A dermatoscopic image of a skin lesion — 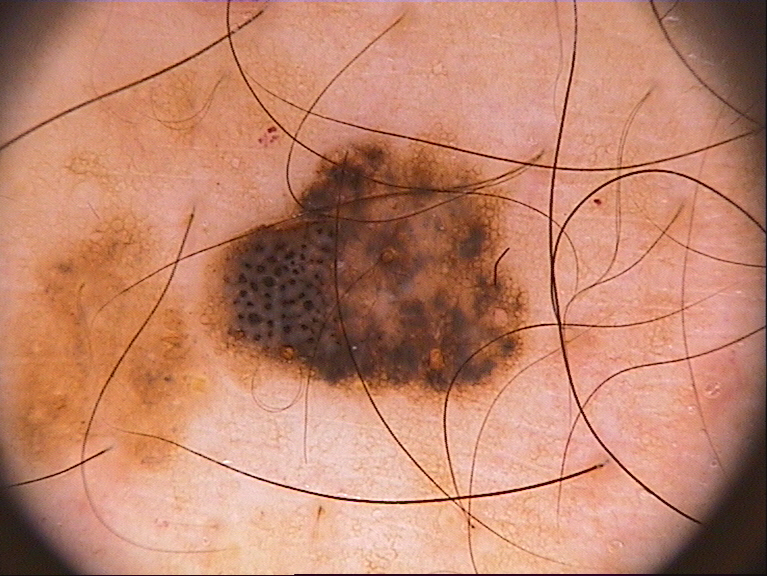Case summary:
- size — ~16% of the field
- dermoscopic features — pigment network and globules; absent: negative network, streaks, and milia-like cysts
- lesion location — box(202, 136, 533, 399)
- diagnosis — a melanocytic nevus